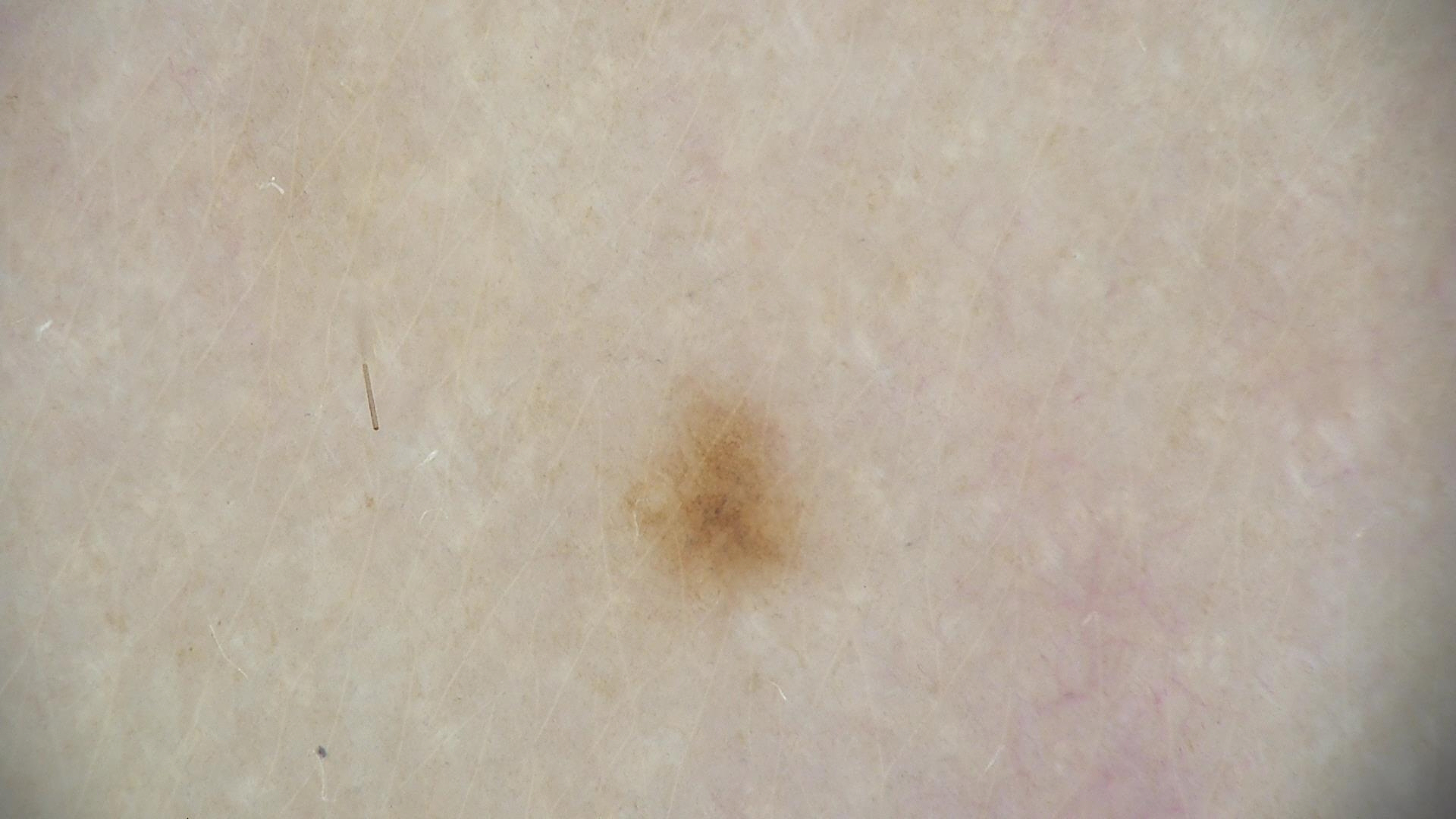Impression:
Diagnosed as a dysplastic junctional nevus.